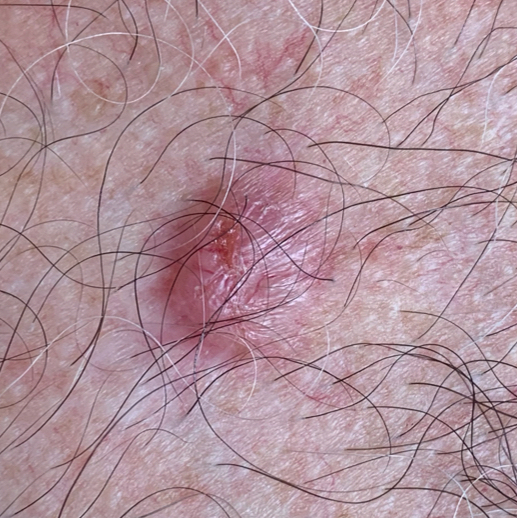By history, prior skin cancer (patient or family) and no tobacco use.
A clinical photograph showing a skin lesion.
A male patient 55 years of age.
The lesion involves the chest.
The lesion measures approximately 13 × 12 mm.
Per patient report, the lesion has grown, itches, and is elevated.
Histopathological examination showed a basal cell carcinoma.